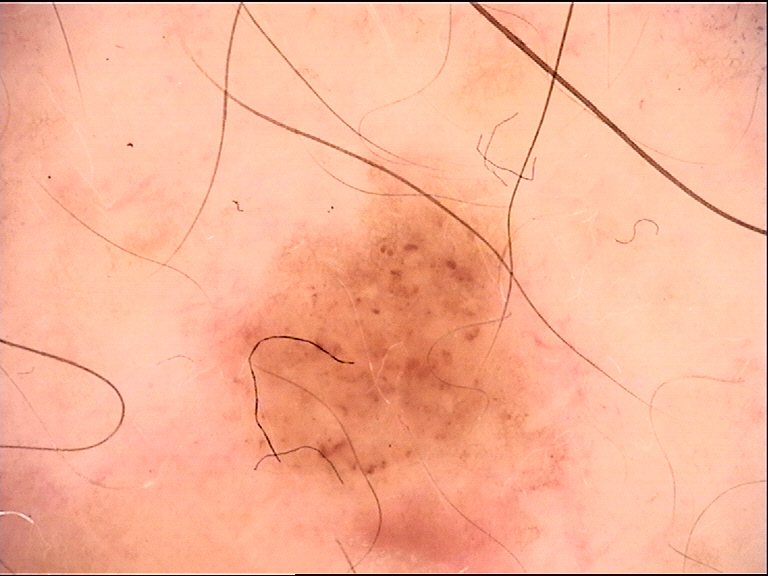A skin lesion imaged with a dermatoscope. Classified as a dysplastic junctional nevus.